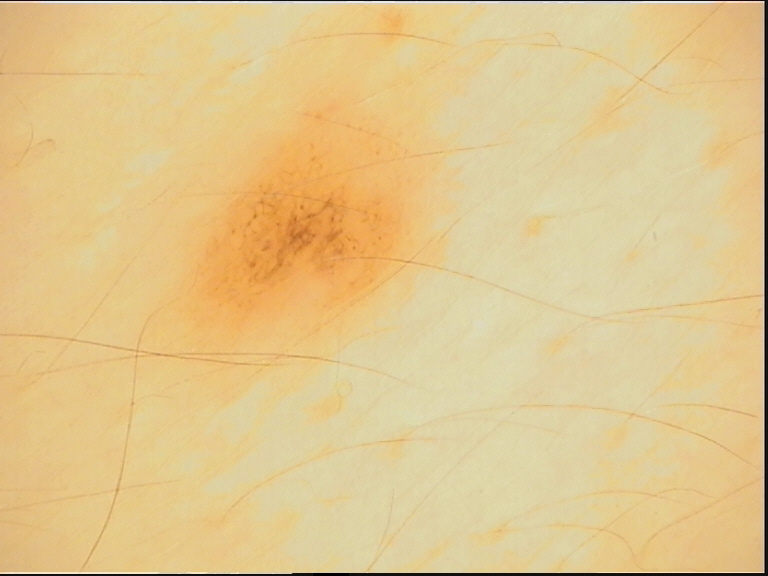Classified as a compound nevus.